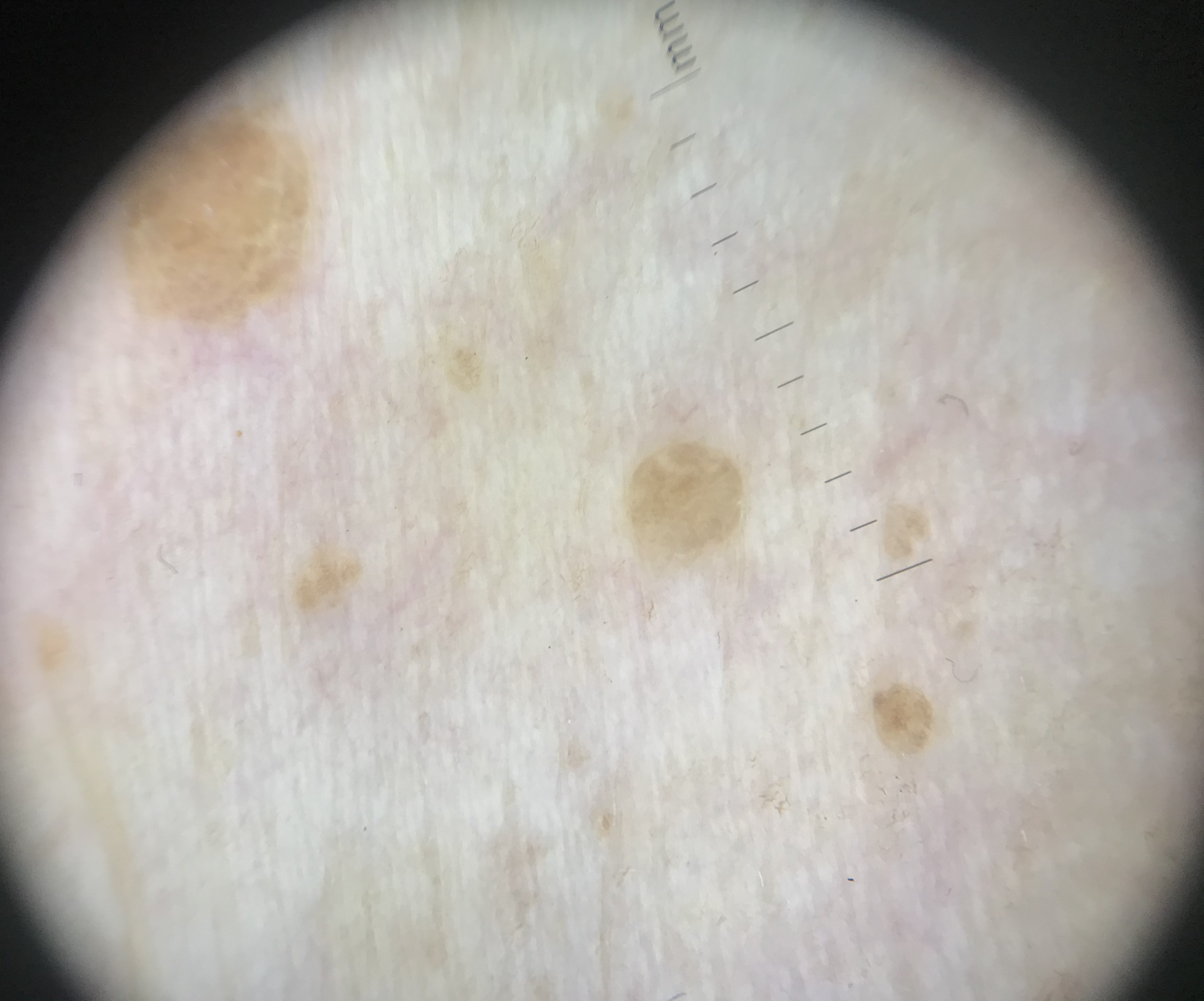A dermoscopic photograph of a skin lesion. Consistent with a keratinocytic lesion — a seborrheic keratosis.